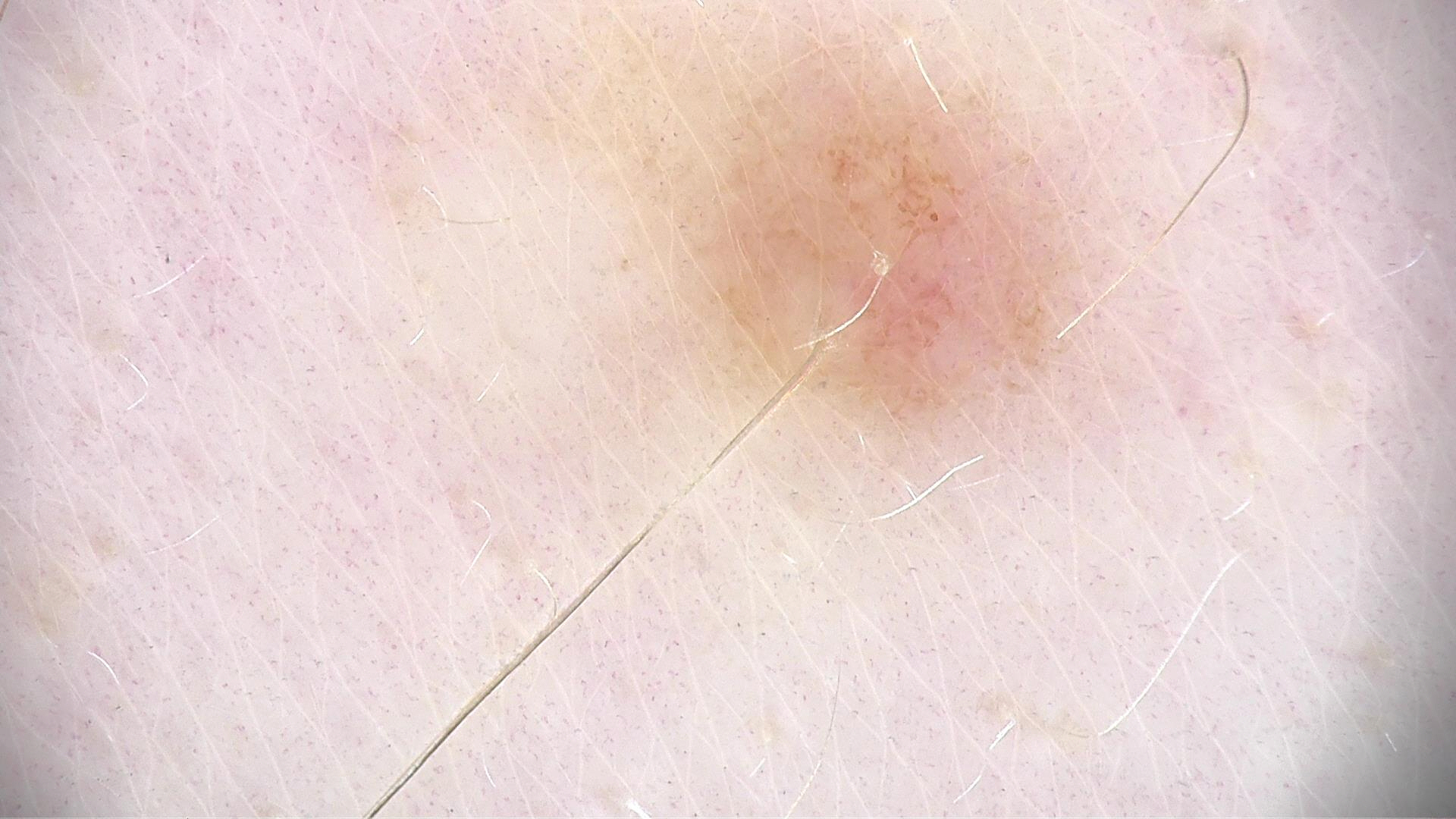Conclusion:
The diagnosis was a dysplastic junctional nevus.